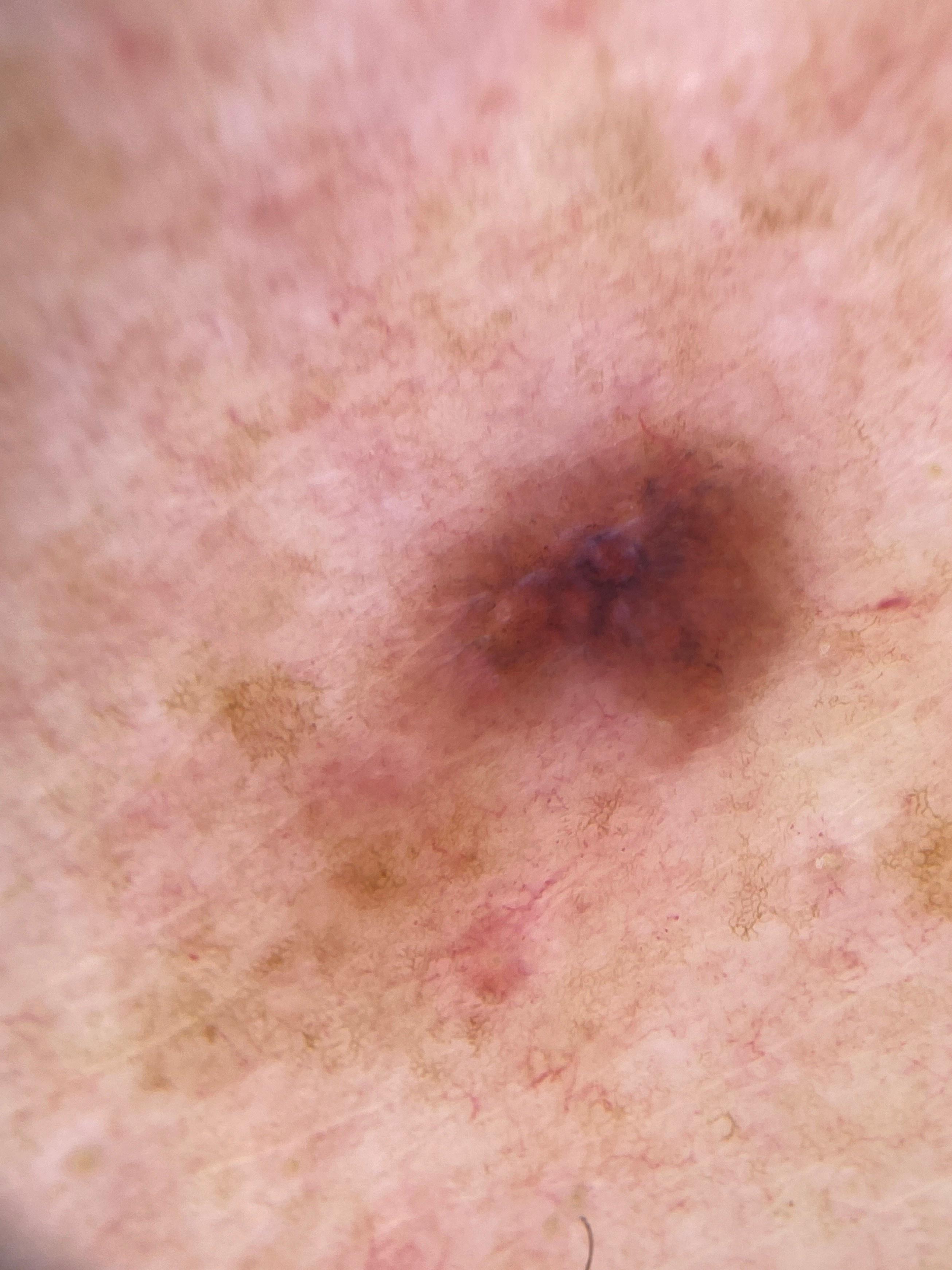Findings:
– FST · II
– image · contact-polarized dermoscopy
– melanoma history · a prior melanoma
– patient · male, approximately 80 years of age
– diagnostic label · Melanoma (biopsy-proven)